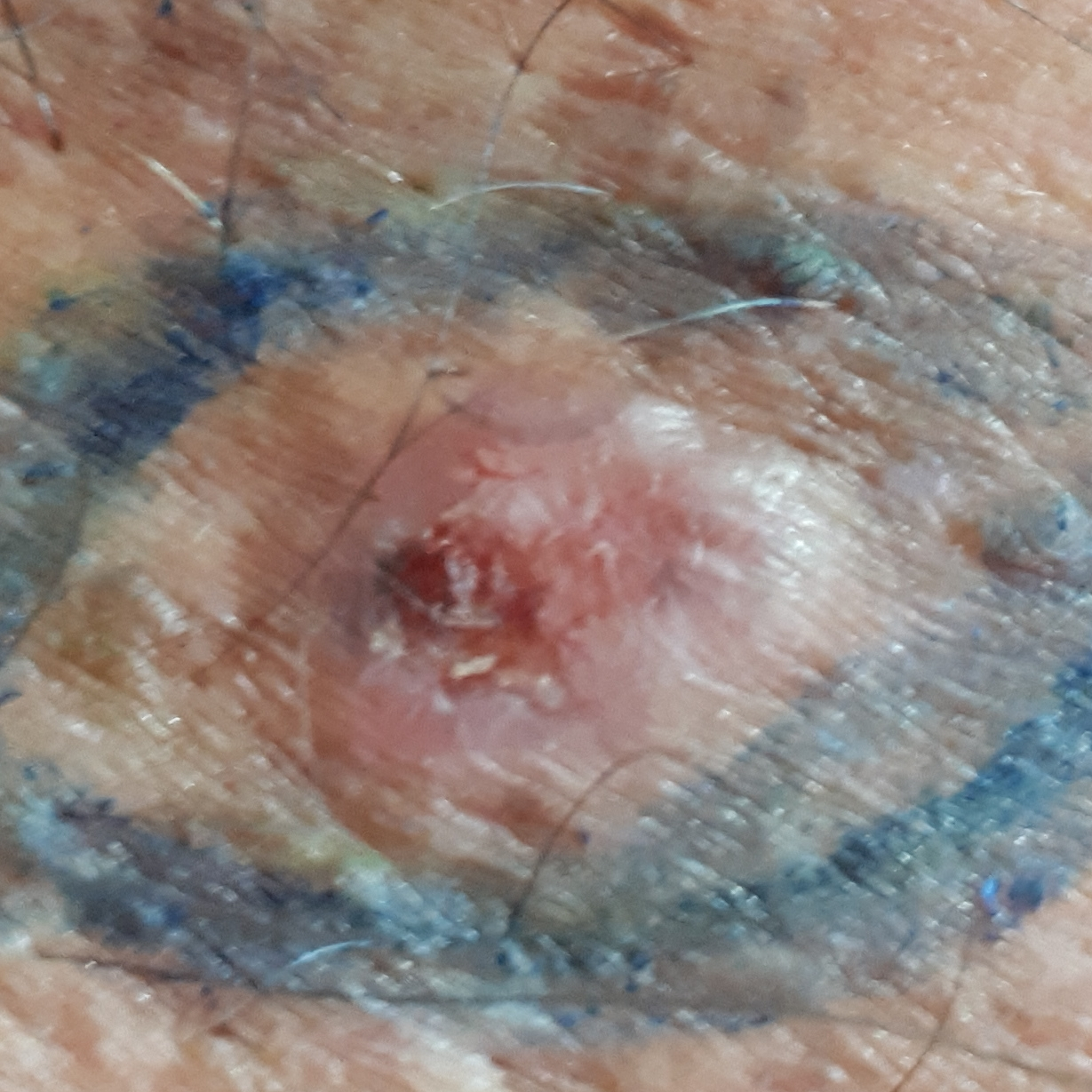Q: What kind of image is this?
A: clinical photo
Q: What does the exposure history note?
A: prior skin cancer (patient or family), pesticide exposure, tobacco use, no prior malignancy (patient or family)
Q: Who is the patient?
A: male, in their mid-60s
Q: What is the patient's skin type?
A: II
Q: How large is the lesion?
A: 12 × 7 mm
Q: What does the patient describe?
A: bleeding, itching, elevation, pain
Q: What is this lesion?
A: basal cell carcinoma (biopsy-proven)